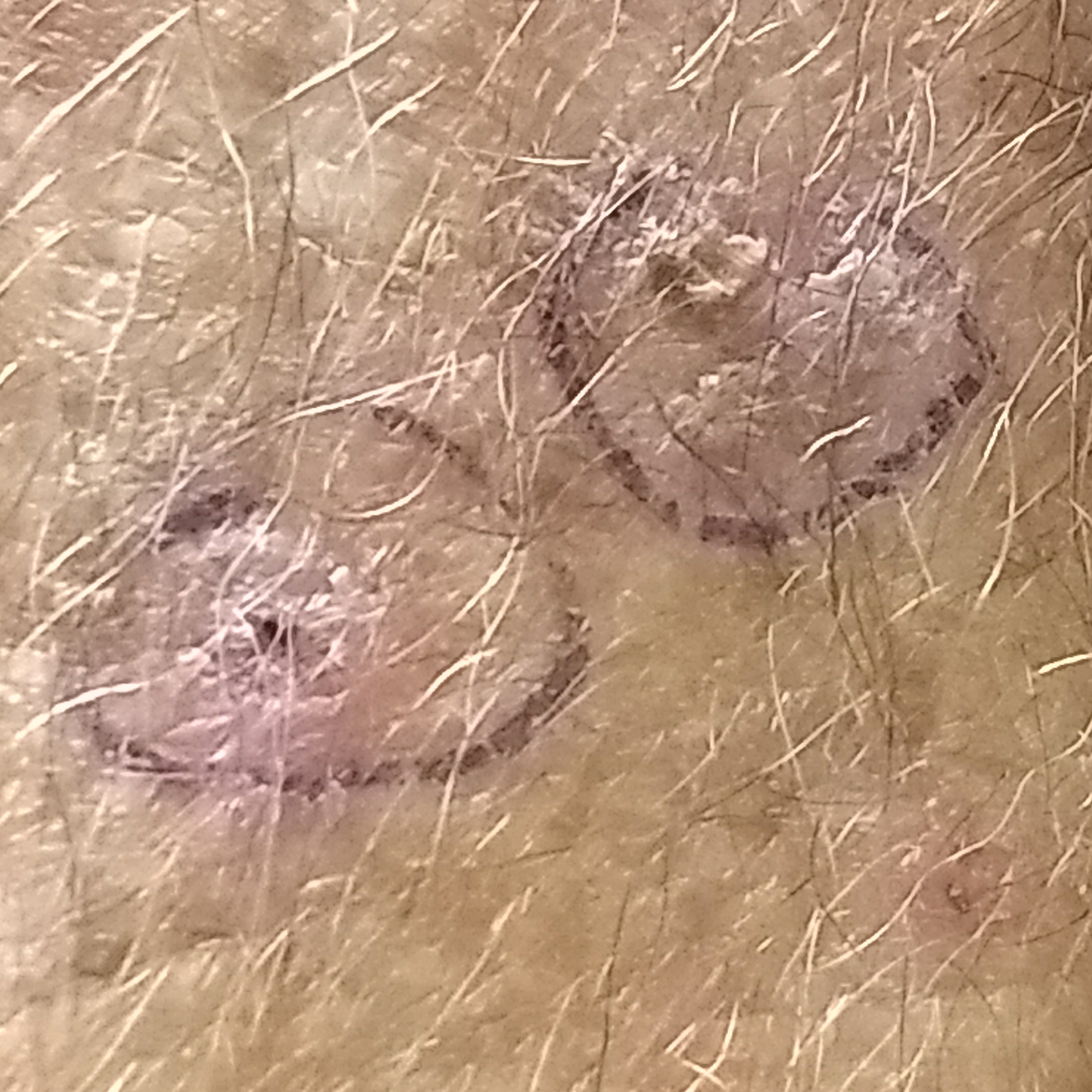Summary: A clinical photo of a skin lesion taken with a smartphone. The lesion was found on a forearm. Impression: Consistent with a premalignant lesion — an actinic keratosis.